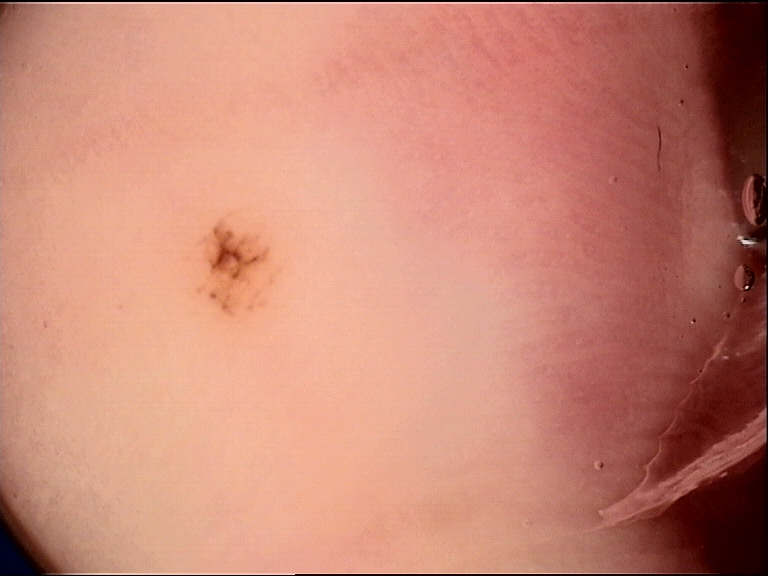A dermoscopic image of a skin lesion. Diagnosed as an acral dysplastic junctional nevus.